A dermatoscopic image of a skin lesion: 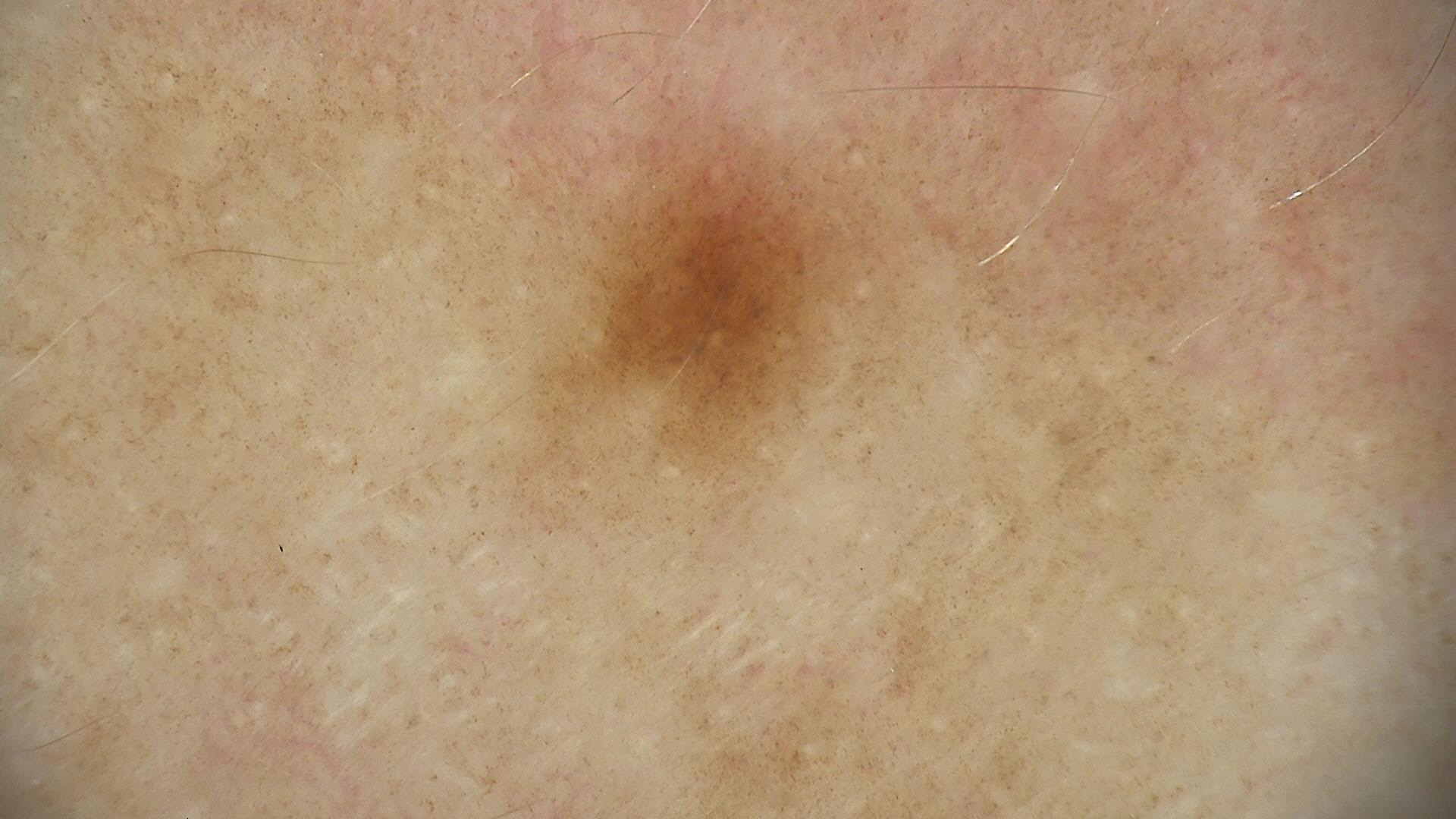The diagnosis was a benign lesion — a dysplastic junctional nevus.